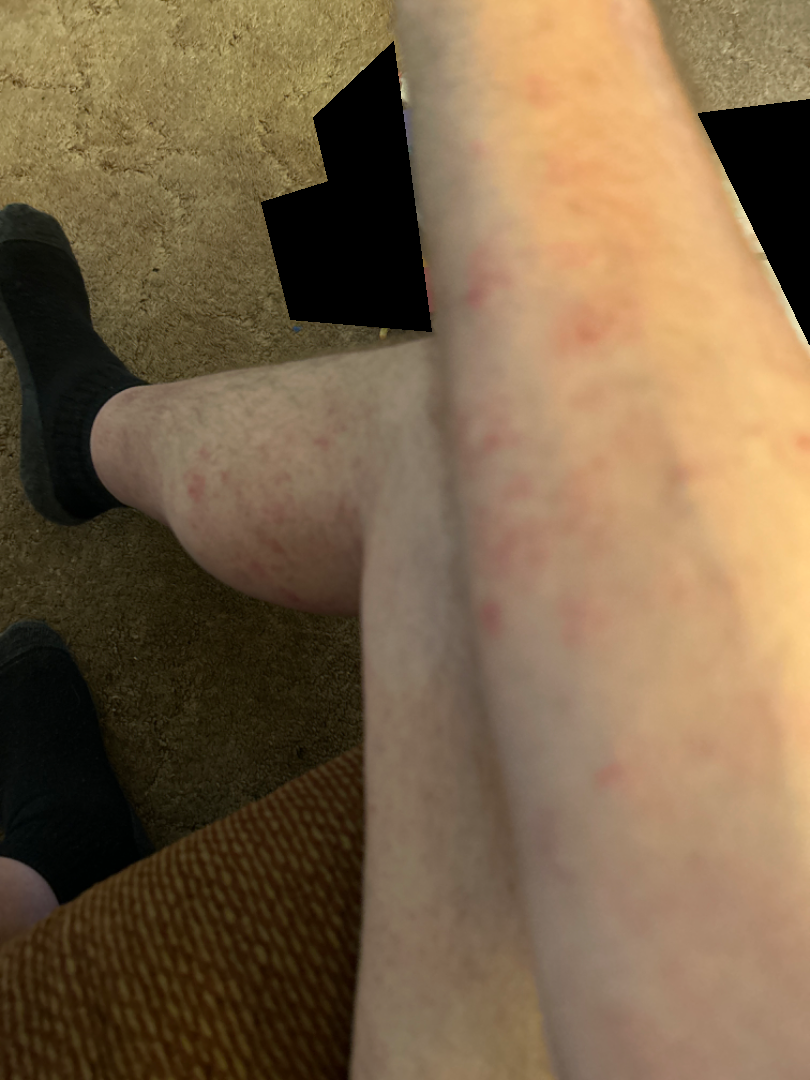Case summary:
- subject: male, age 50–59
- texture: rough or flaky and flat
- framing: at a distance
- lesion symptoms: burning, bothersome appearance and itching
- skin tone: Fitzpatrick skin type IV; non-clinician graders estimated Monk Skin Tone 3
- self-categorized as: a rash
- location: leg, back of the hand, palm and arm
- differential diagnosis: Pigmented purpuric eruption (most likely)